This image was taken at an angle — 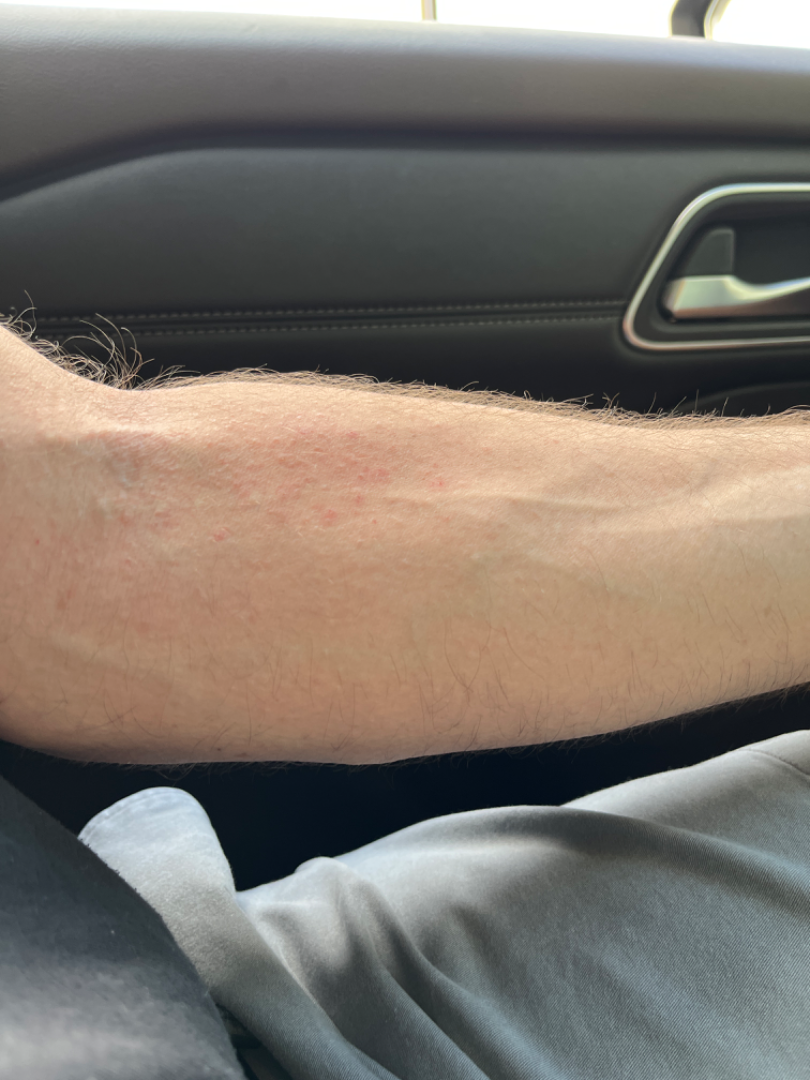  differential:
    leading:
      - Eczema
    considered:
      - Drug Rash
      - Allergic Contact Dermatitis